The patient is a female about 30 years old · a dermatoscopic image of a skin lesion.
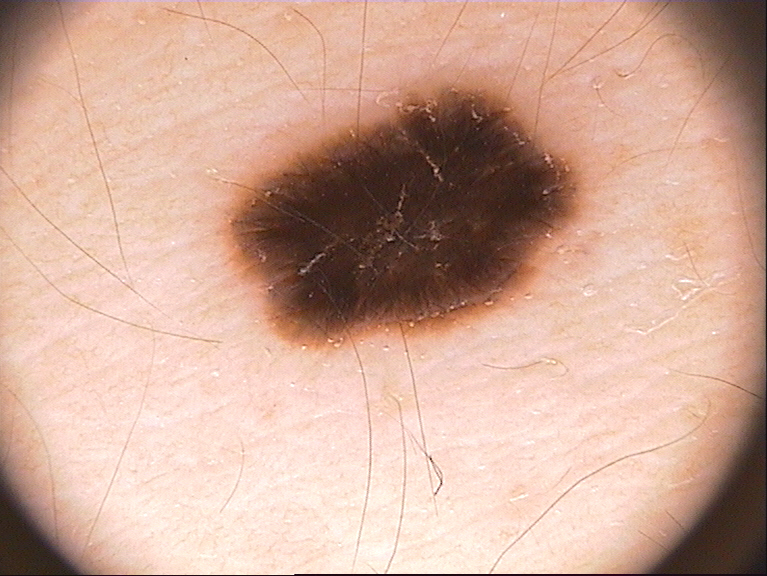The dermoscopic pattern shows no milia-like cysts, streaks, negative network, pigment network, or globules. The visible lesion spans box(219, 68, 595, 349). Diagnosed as a melanocytic nevus, a benign skin lesion.